A male subject in their late 50s; recorded as Fitzpatrick III; a clinical photo of a skin lesion taken with a smartphone: 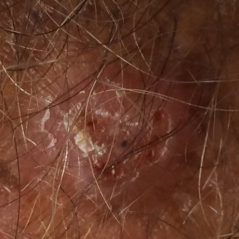The lesion is on a forearm. The lesion measures approximately 12 × 10 mm. By the patient's account, the lesion is elevated, itches, hurts, and has bled. The biopsy diagnosis was a basal cell carcinoma.